A clinical photograph showing a skin lesion; the patient says their skin tans without first burning; by self-report, a history of sunbed use; a female subject 47 years old; the patient describes having a moderate number of moles; acquired for a research image collection, with no referral diagnosis — 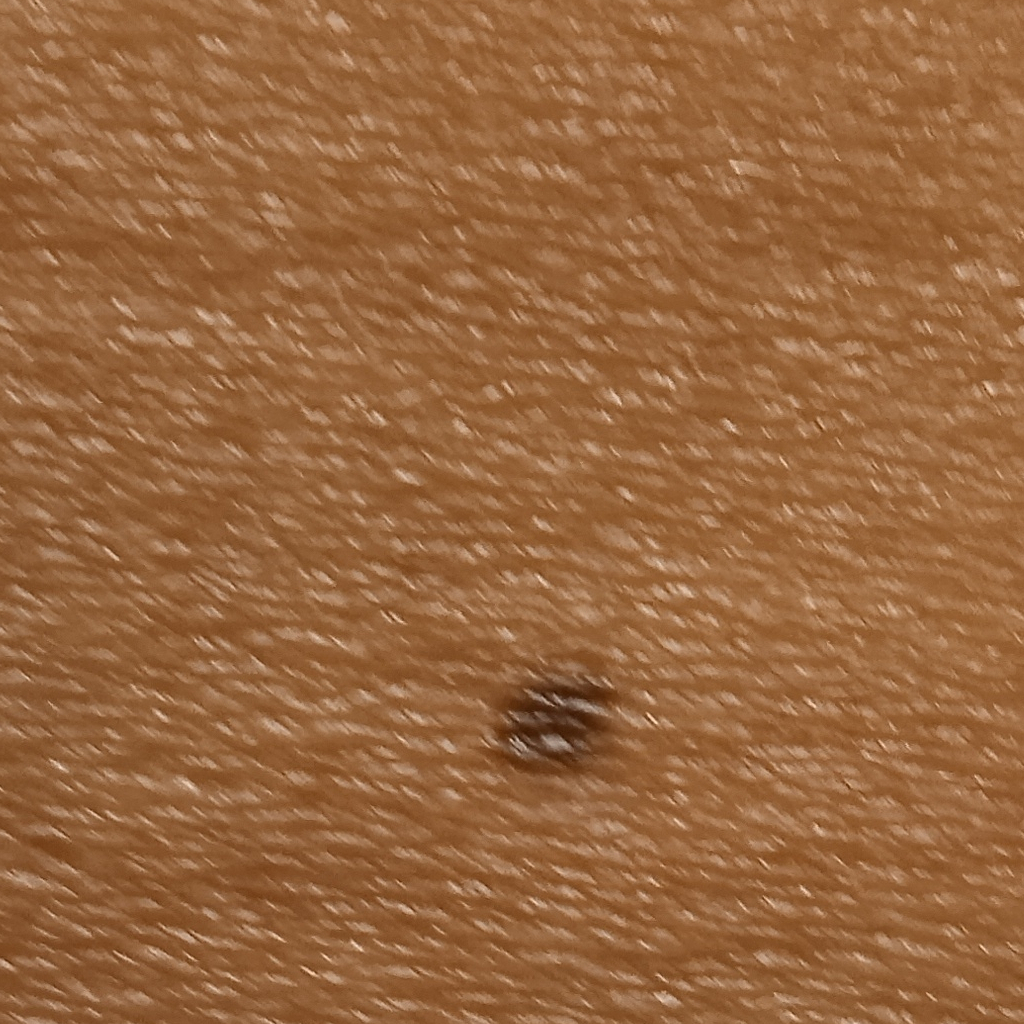Clinical context:
Located on an arm.
Impression:
The dermatologists' assessment was a melanocytic nevus.